Reported lesion symptoms include bothersome appearance and itching; the contributor is a female aged 40–49; present for one to four weeks; the patient also reports fatigue and shortness of breath; the lesion involves the head or neck and arm; an image taken at an angle: 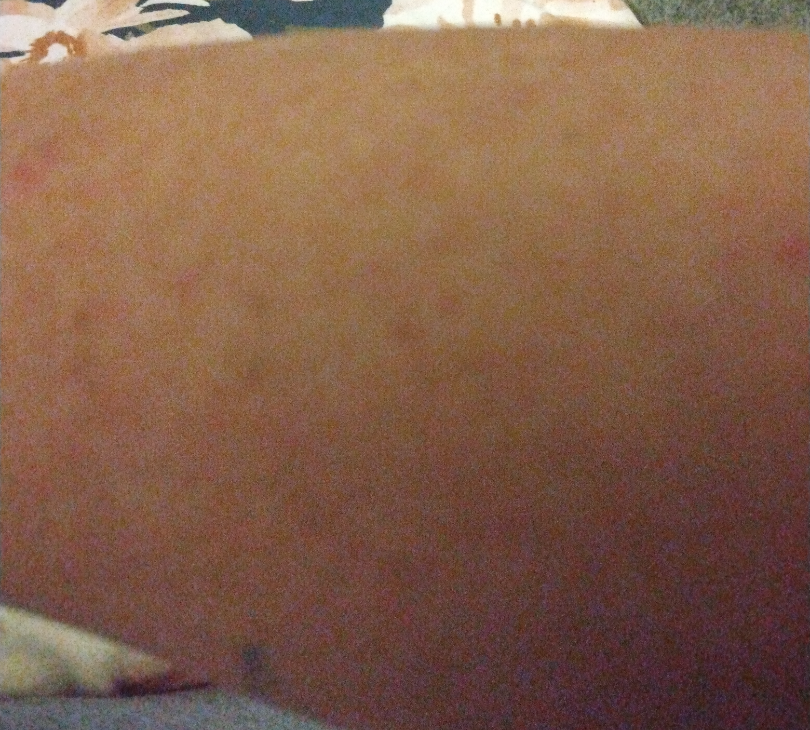Impression:
The reviewer was unable to grade this case for skin condition.